This image was taken at a distance — 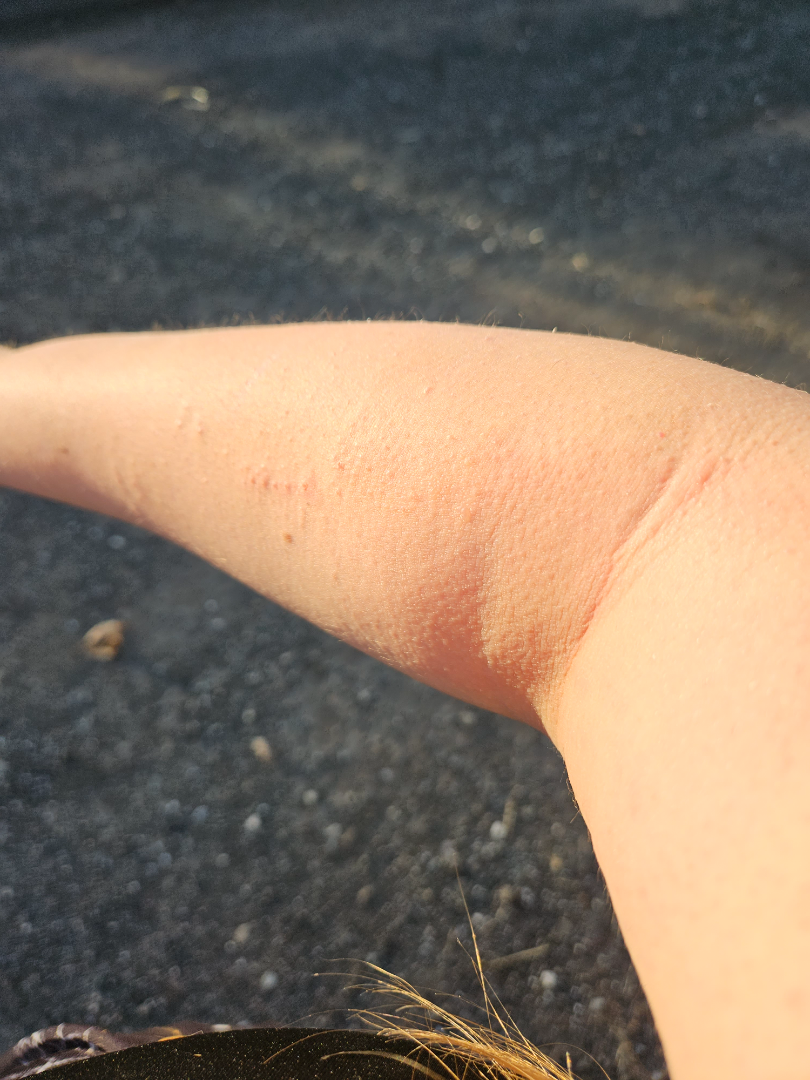Keratosis pilaris (considered); Eczema (considered); Allergic Contact Dermatitis (considered).